An image taken at an angle. The affected area is the arm, leg, front of the torso, back of the torso and top or side of the foot:
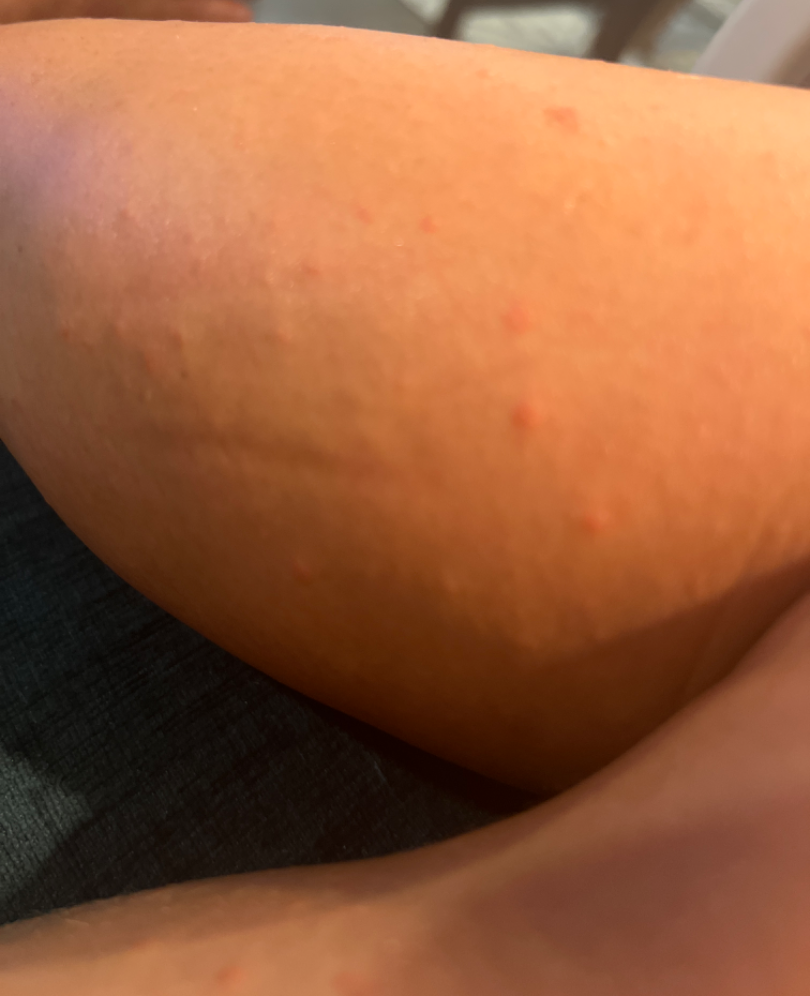- assessment — indeterminate
- patient describes the issue as — a rash
- onset — one to four weeks
- texture — raised or bumpy and rough or flaky
- reported symptoms — itching, bothersome appearance and enlargement